A dermoscopic image of a skin lesion · imaged for a research study, with no referral diagnosis recorded · a female subject 48 years old.
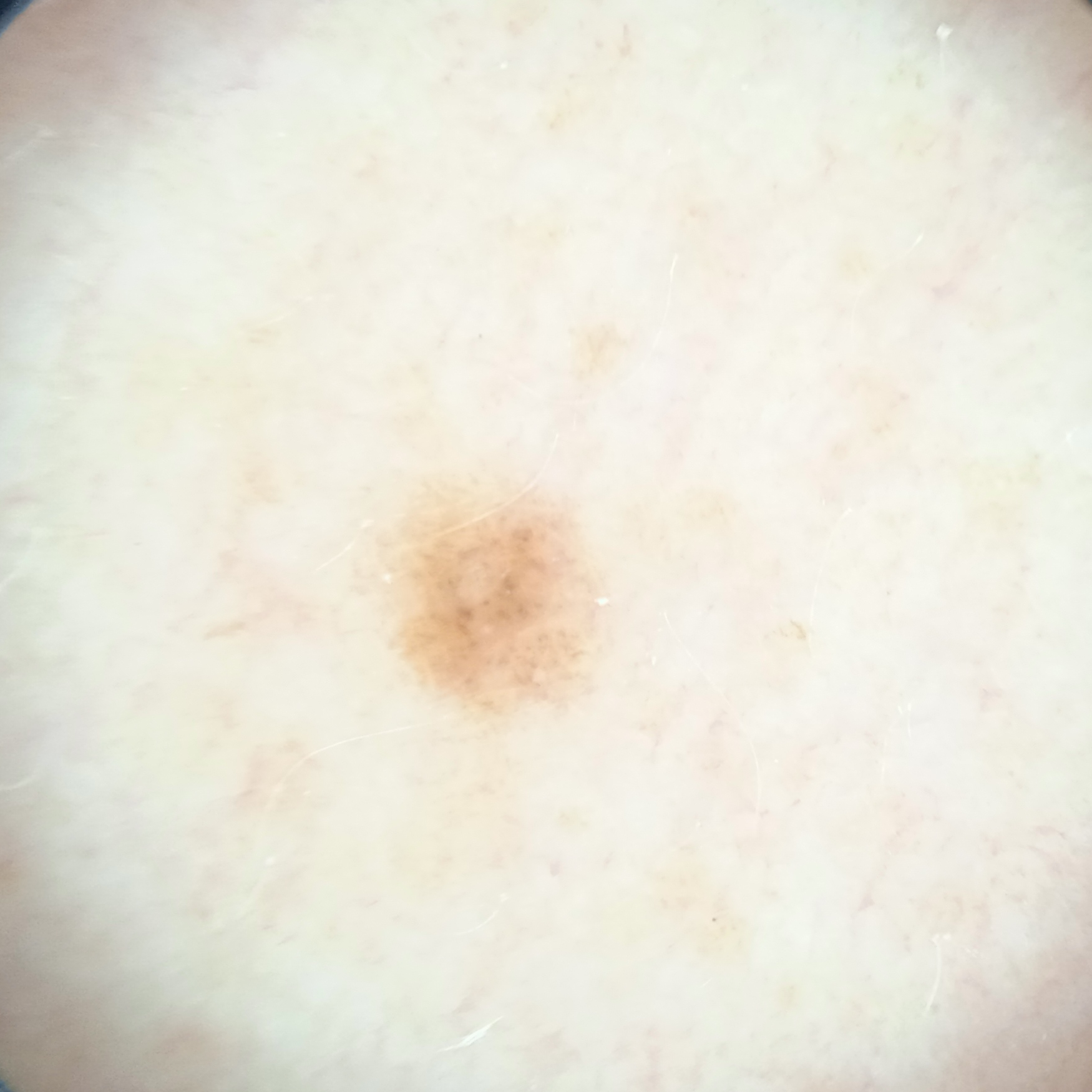The lesion is located on an arm.
Measuring roughly 2.7 mm.
The consensus diagnosis for this lesion was a melanocytic nevus.